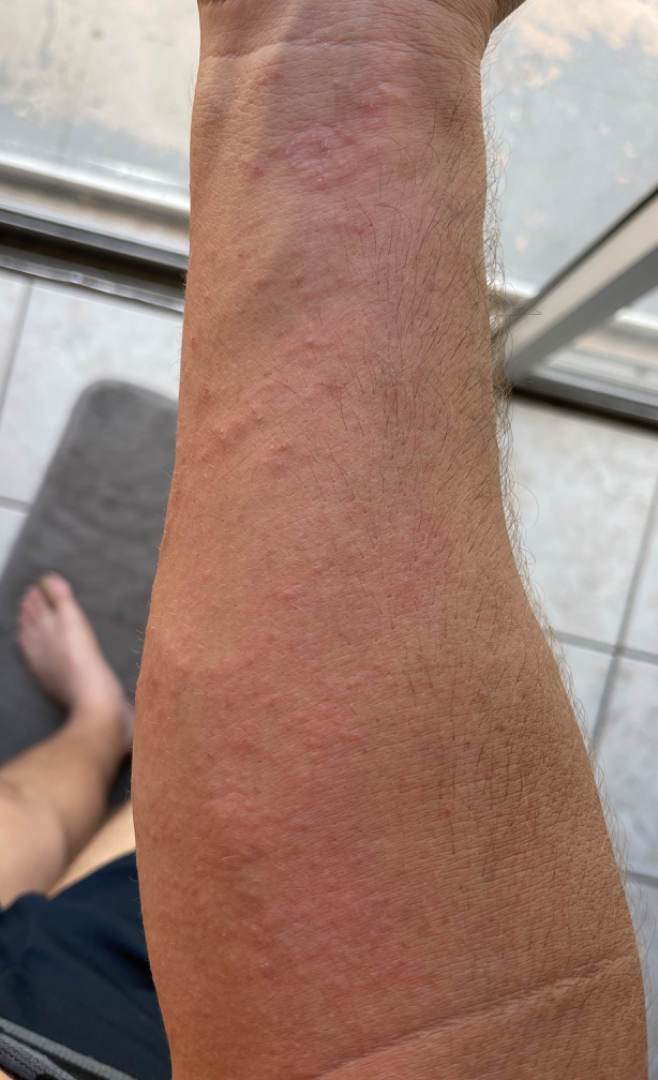Findings:
• patient · male
• symptoms · itching, bothersome appearance and burning
• affected area · arm
• self-categorized as · a rash
• framing · at a distance
• surface texture · raised or bumpy
• impression · reviewed remotely by three dermatologists: the differential is split between Acute dermatitis, NOS; Eczema; and Contact dermatitis; less likely is Allergic Contact Dermatitis